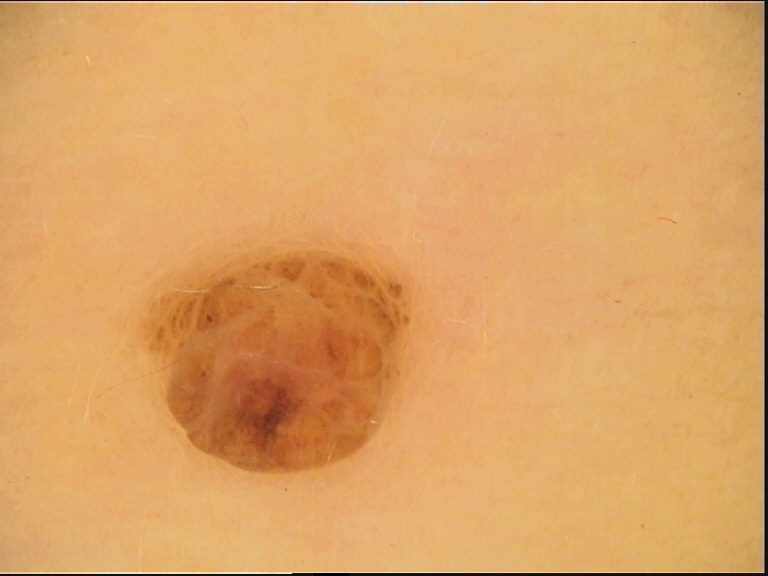<lesion>
  <image>dermoscopy</image>
  <lesion_type>
    <main_class>banal</main_class>
    <pattern>dermal</pattern>
  </lesion_type>
  <diagnosis>
    <name>dermal nevus</name>
    <code>db</code>
    <malignancy>benign</malignancy>
    <super_class>melanocytic</super_class>
    <confirmation>expert consensus</confirmation>
  </diagnosis>
</lesion>